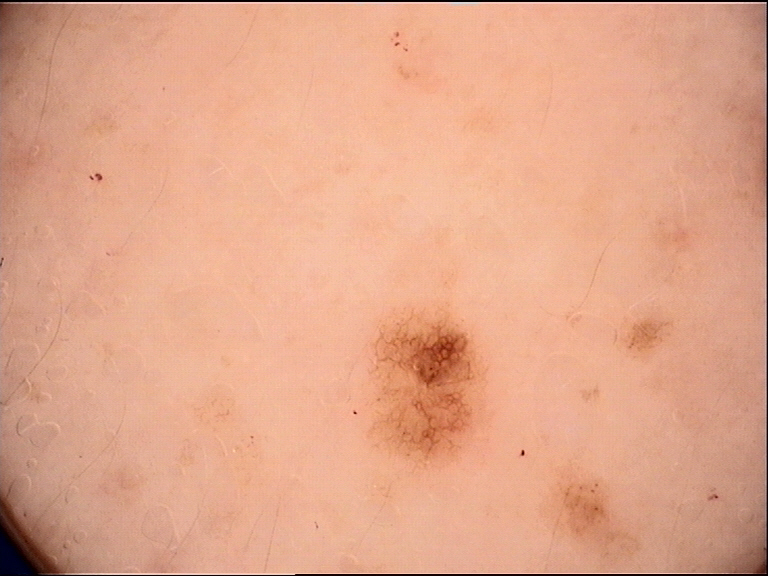Q: What is the diagnosis?
A: dysplastic junctional nevus (expert consensus)